The photo was captured at an angle; female patient, age 18–29; located on the arm.
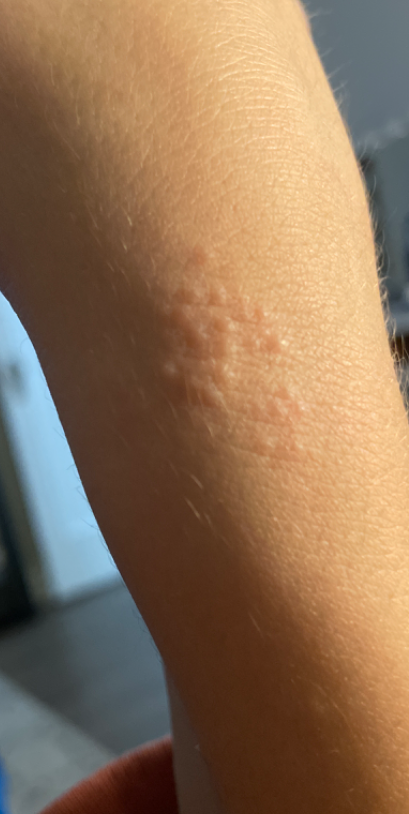The patient reports bothersome appearance. The patient reports the condition has been present for one to four weeks. Fitzpatrick IV; human graders estimated a Monk Skin Tone of 3. The patient considered this a rash. The lesion is described as raised or bumpy. The patient reported no systemic symptoms. The reviewing dermatologist's impression was: favoring Allergic Contact Dermatitis; the differential also includes Eczema; also consider Irritant Contact Dermatitis.